The patient is a male aged approximately 65 · a skin lesion imaged with a dermatoscope.
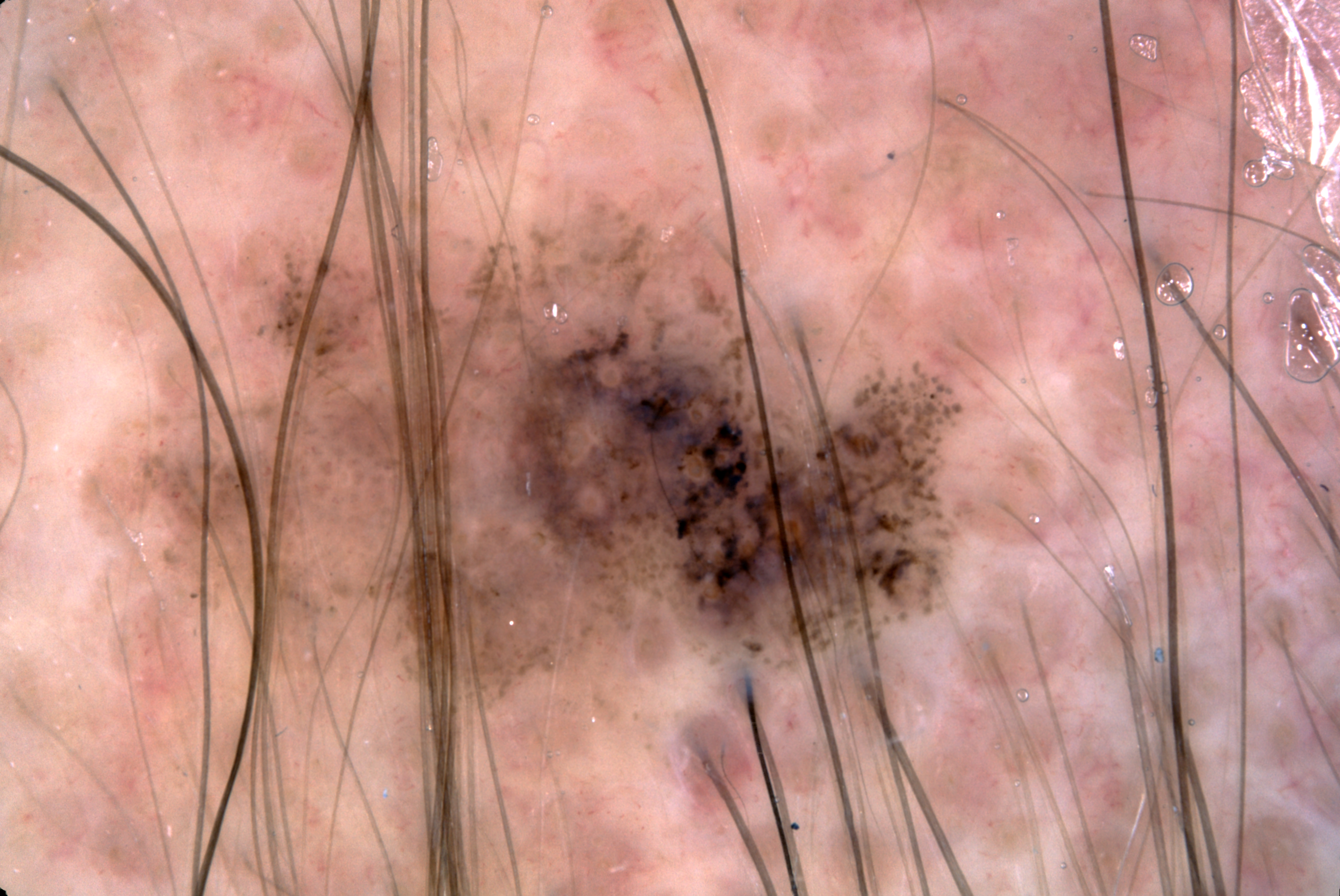In (x1, y1, x2, y2) order, the lesion spans bbox=[66, 150, 1009, 855]. Dermoscopy demonstrates negative network, with no pigment network, milia-like cysts, or streaks. Confirmed on histopathology as a melanoma, a malignant skin lesion.